A dermoscopic image of a skin lesion.
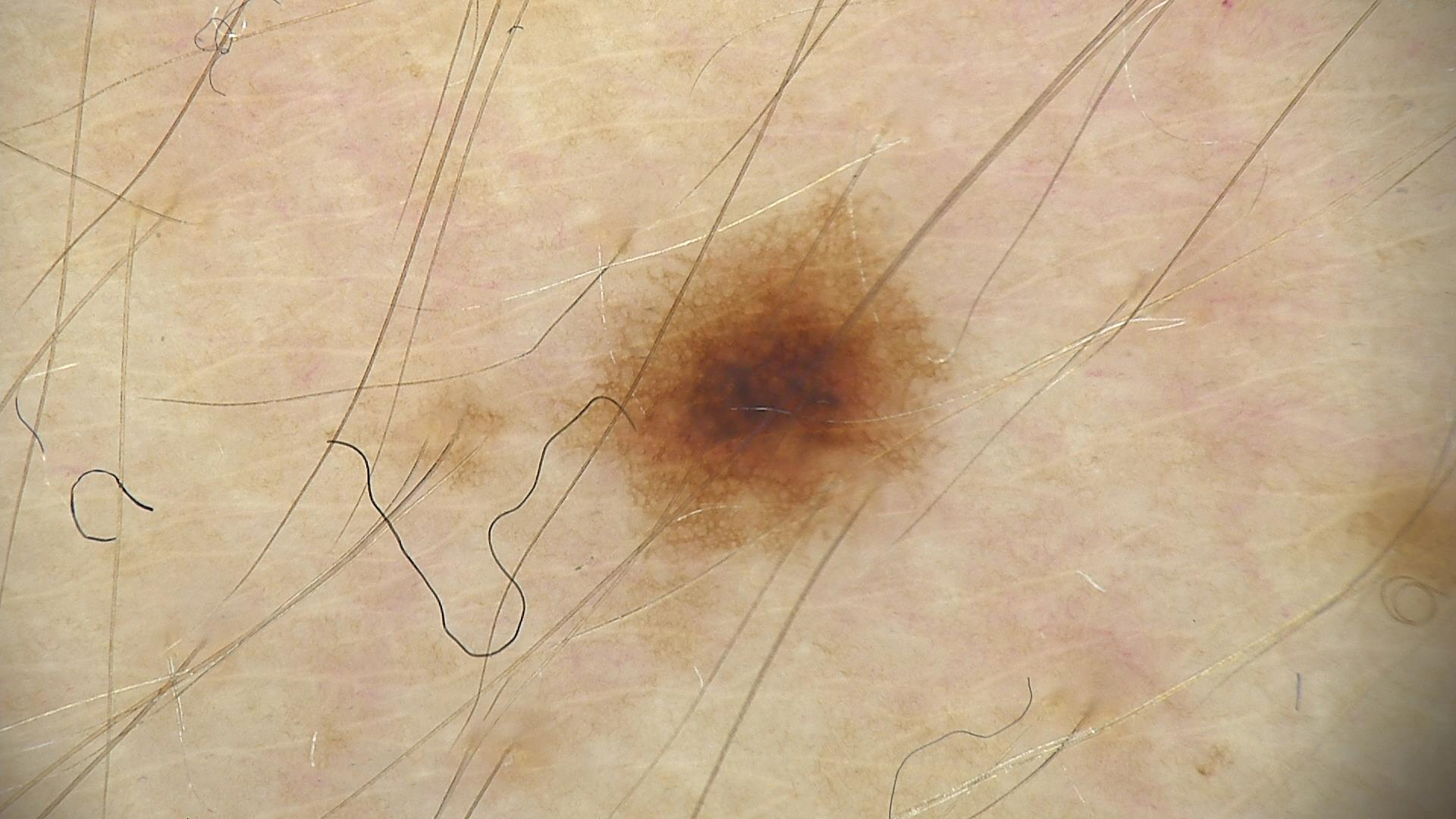Impression:
Diagnosed as a benign lesion — a dysplastic junctional nevus.